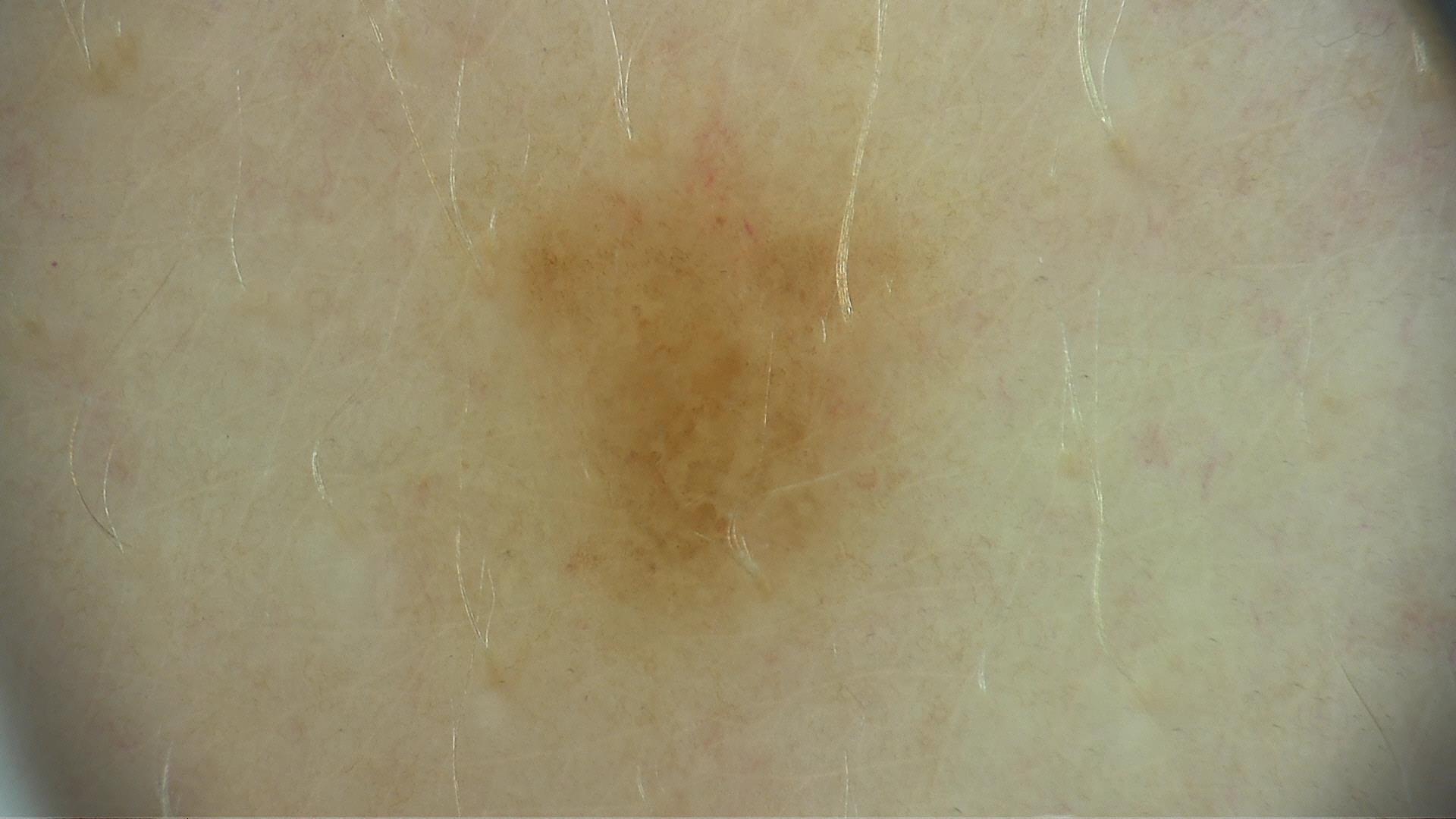Labeled as a dysplastic junctional nevus.